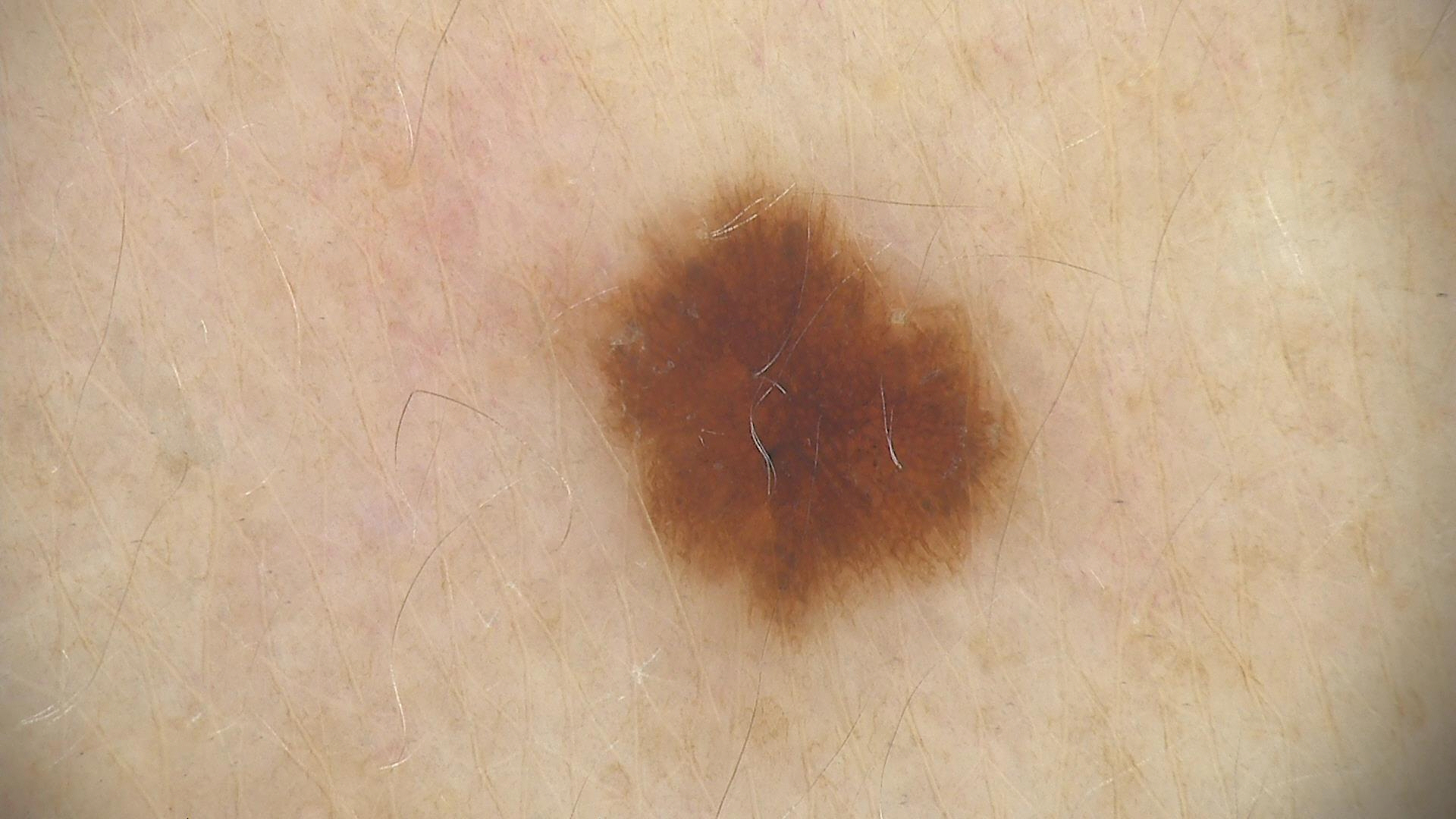Case:
– imaging — dermatoscopy
– assessment — dysplastic junctional nevus (expert consensus)